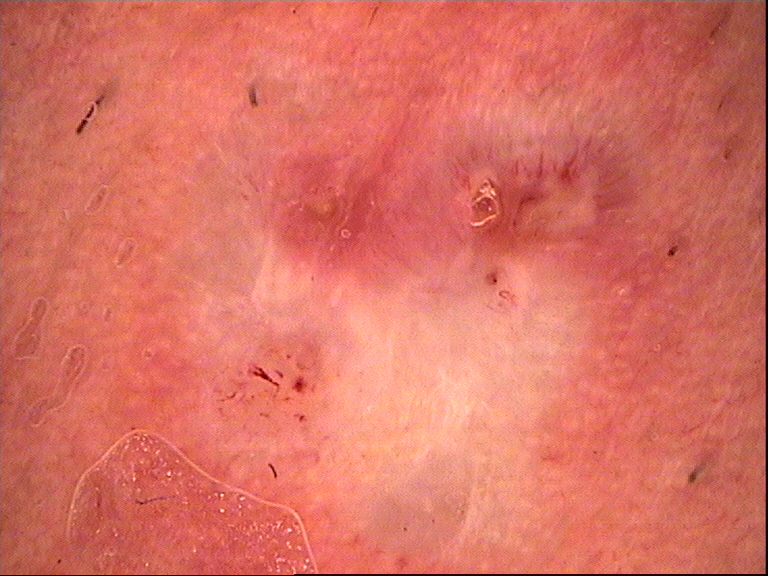Histopathologically confirmed as a keratinocytic lesion — a basal cell carcinoma.